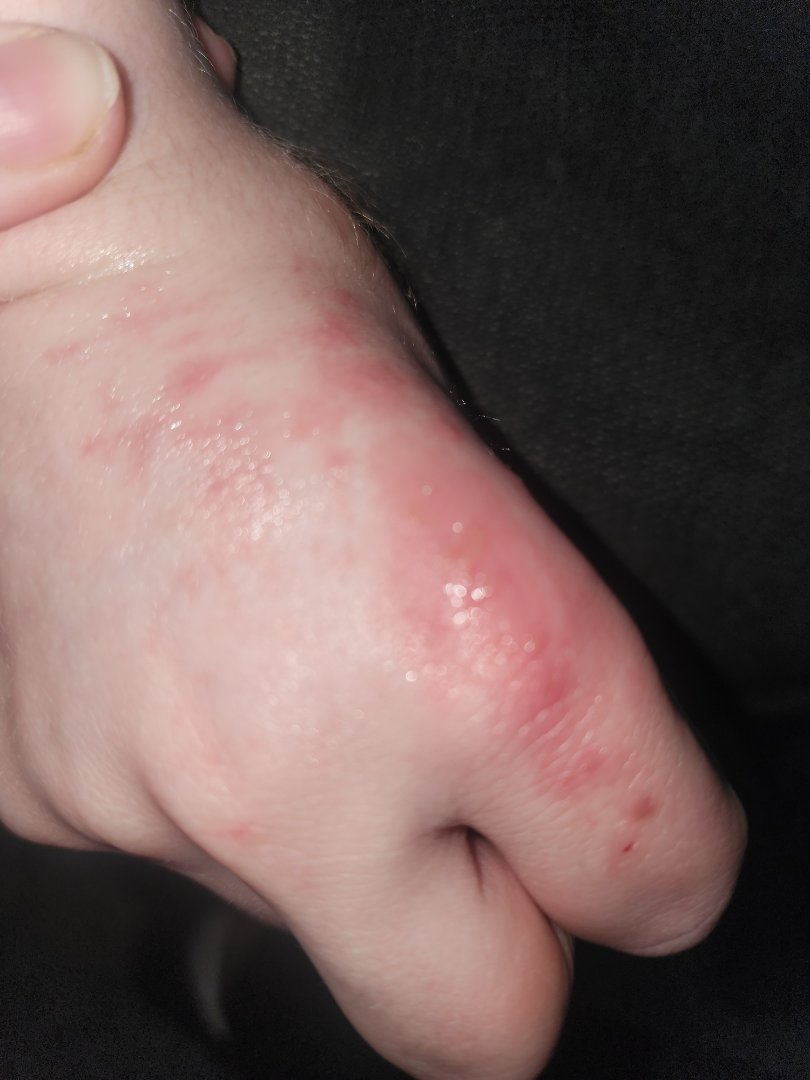History: This is a close-up image. Impression: On dermatologist assessment of the image: Eczema (1.00).